This is a close-up image. The patient is a female aged 18–29. The affected area is the leg and head or neck: 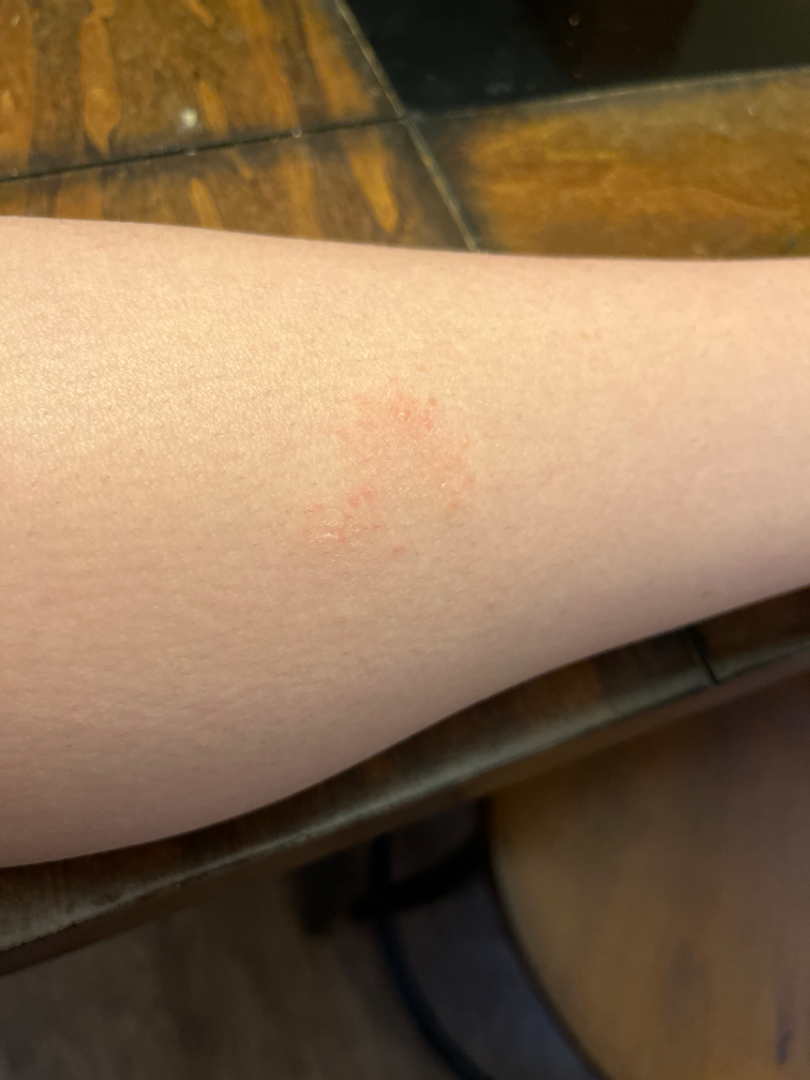Q: What conditions are considered?
A: Xerosis, Eczema and Irritant Contact Dermatitis were each considered, in no particular order